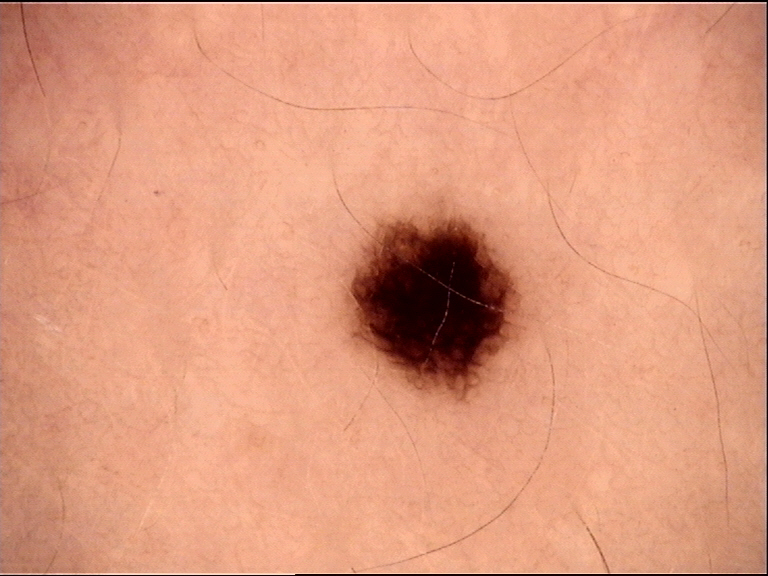Impression:
The diagnostic label was a benign lesion — a dysplastic junctional nevus.